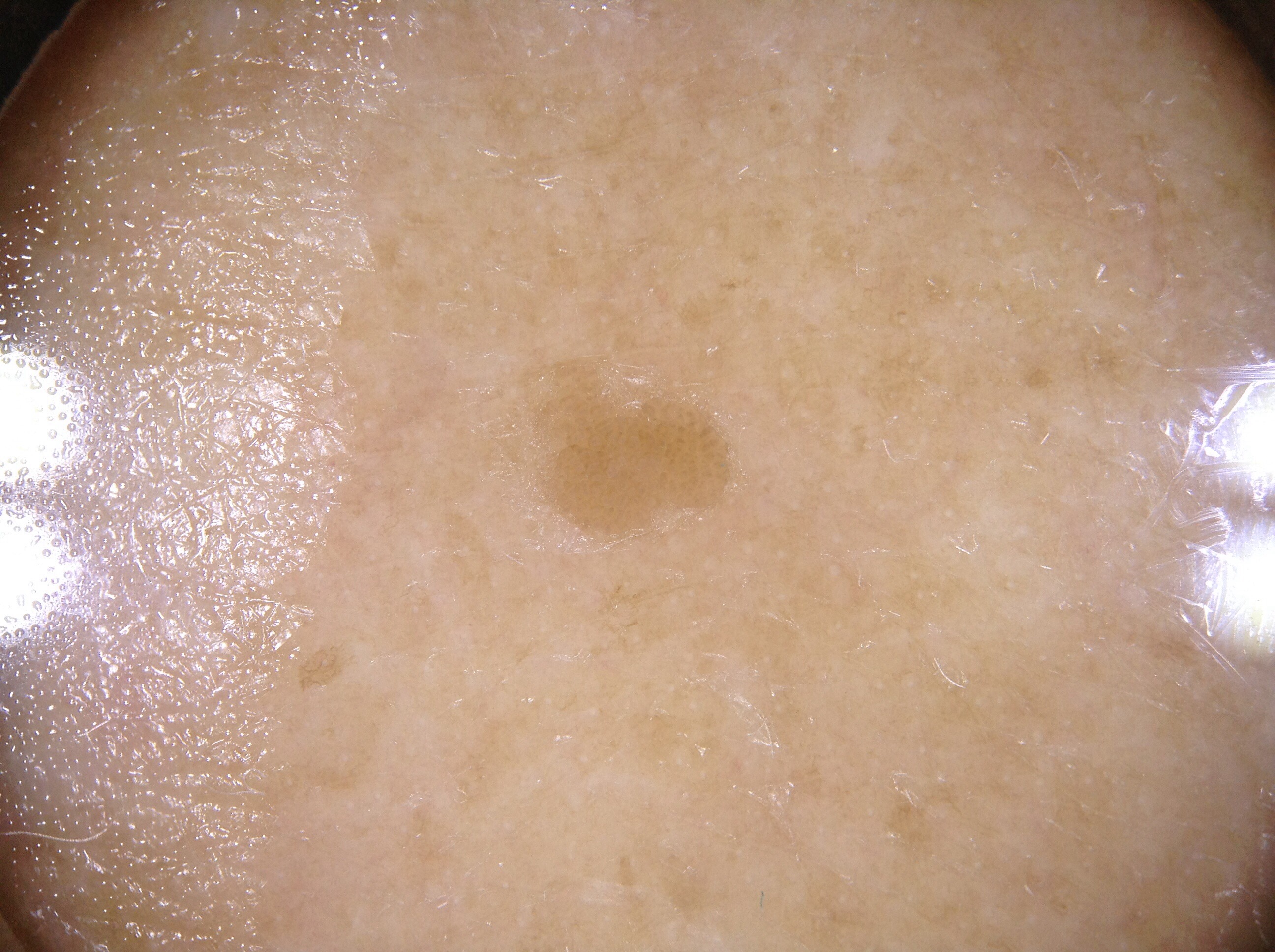Case summary:
- image · dermoscopic image
- lesion location · bbox(568, 409, 717, 513)
- impression · a seborrheic keratosis, a benign skin lesion